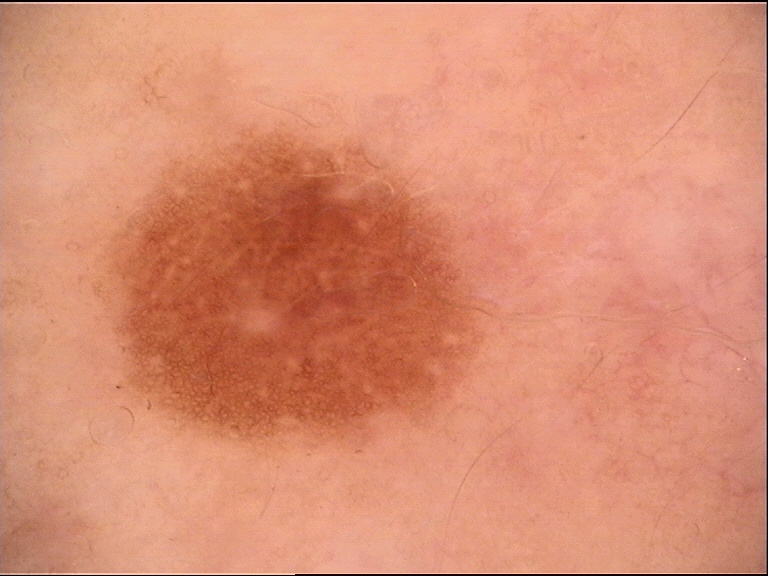The diagnosis was a dysplastic junctional nevus.